A skin lesion imaged with a dermatoscope. A male patient aged 43-47: 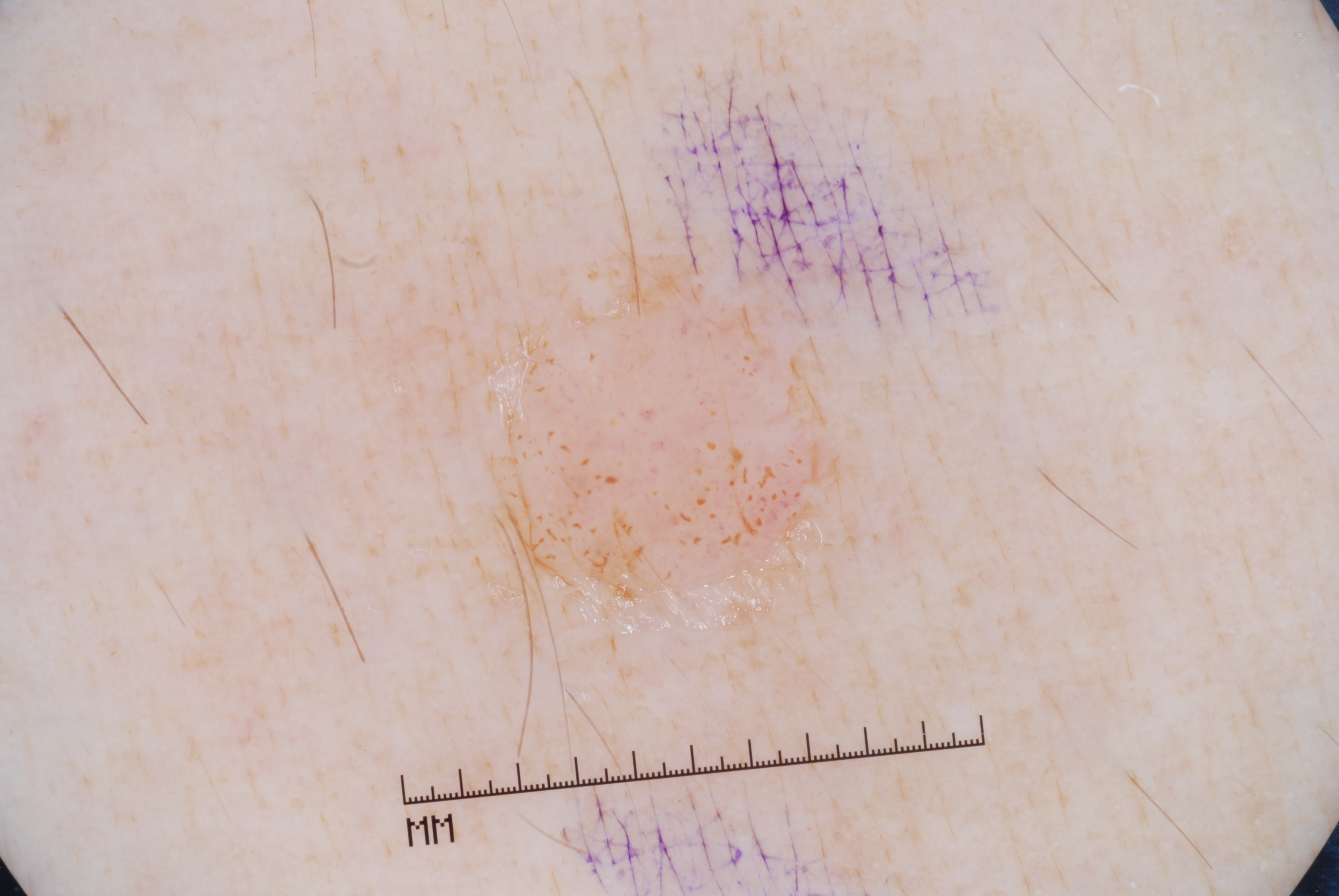<lesion>
  <lesion_location>
    <bbox_xyxy>479, 240, 829, 610</bbox_xyxy>
  </lesion_location>
  <lesion_extent>moderate</lesion_extent>
  <dermoscopic_features>
    <present>milia-like cysts</present>
    <absent>streaks, negative network, pigment network</absent>
  </dermoscopic_features>
  <diagnosis>
    <name>melanocytic nevus</name>
    <malignancy>benign</malignancy>
    <lineage>melanocytic</lineage>
    <provenance>clinical</provenance>
  </diagnosis>
</lesion>